A female patient aged 46; a smartphone photograph of a skin lesion; the chart notes no prior malignancy (patient or family) and no tobacco use; Fitzpatrick phototype II.
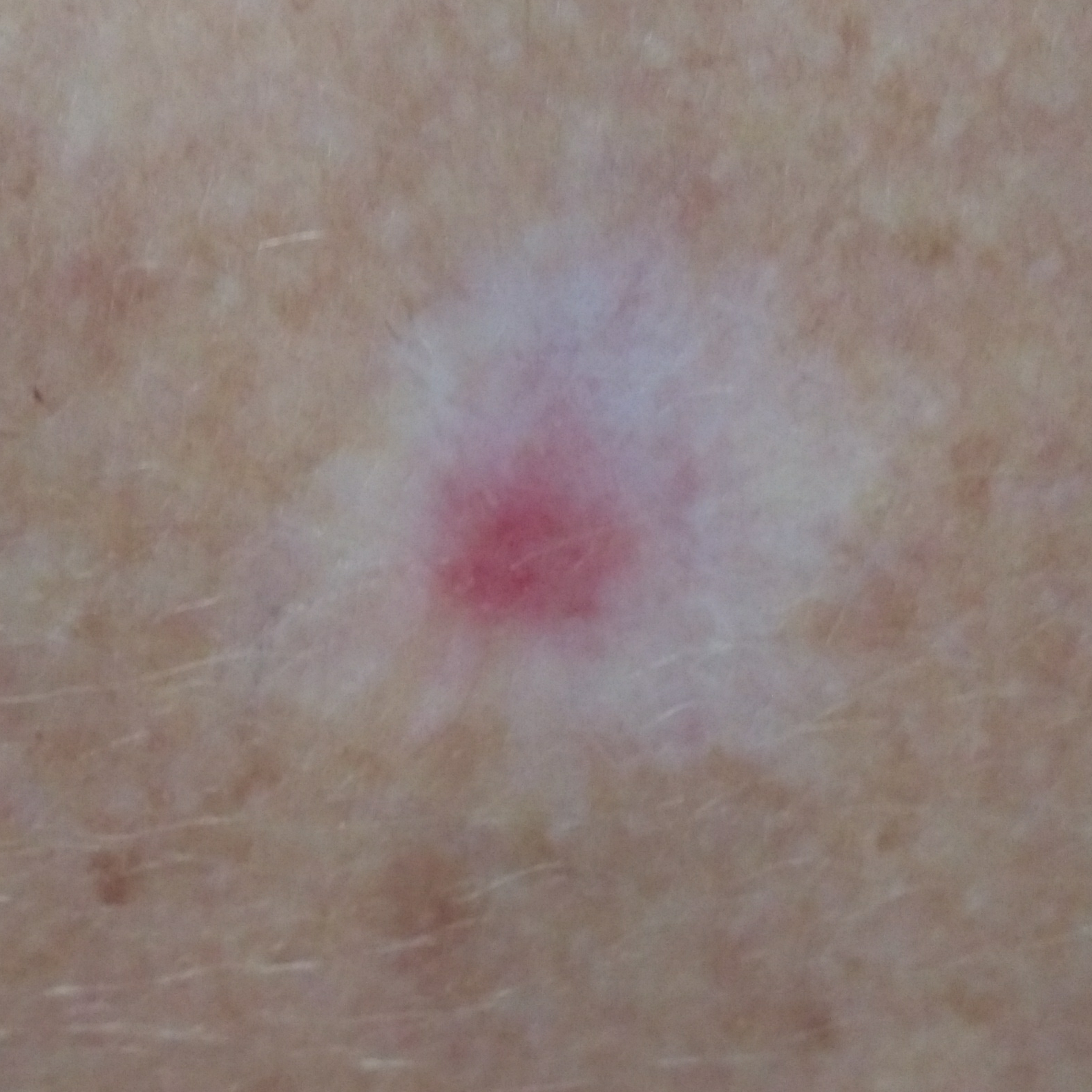Q: Where on the body is the lesion?
A: a forearm
Q: Lesion size?
A: 6x5 mm
Q: What is this lesion?
A: squamous cell carcinoma (biopsy-proven)